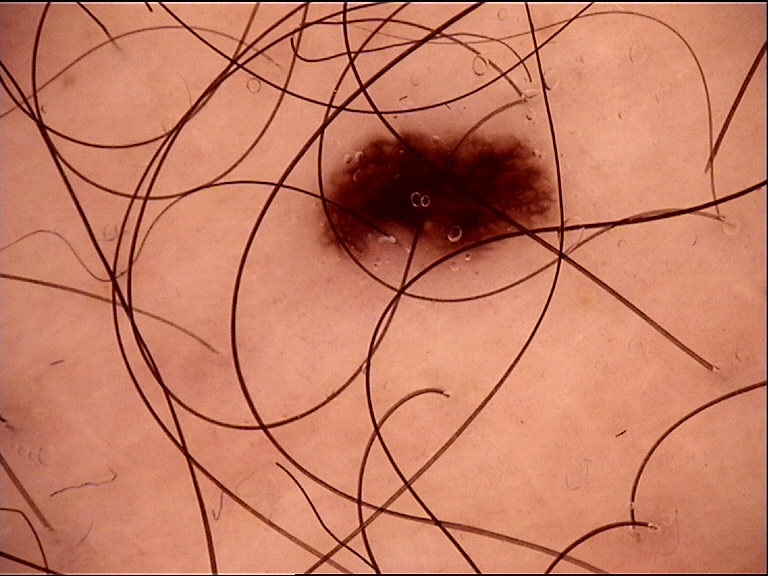Q: What kind of image is this?
A: dermoscopy
Q: How is the lesion classified?
A: banal
Q: What was the diagnostic impression?
A: junctional nevus (expert consensus)